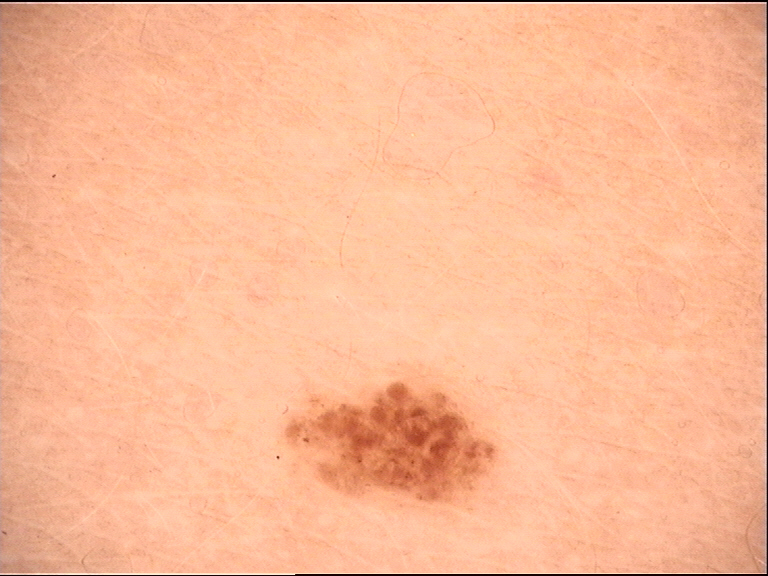Diagnosed as a dysplastic junctional nevus.